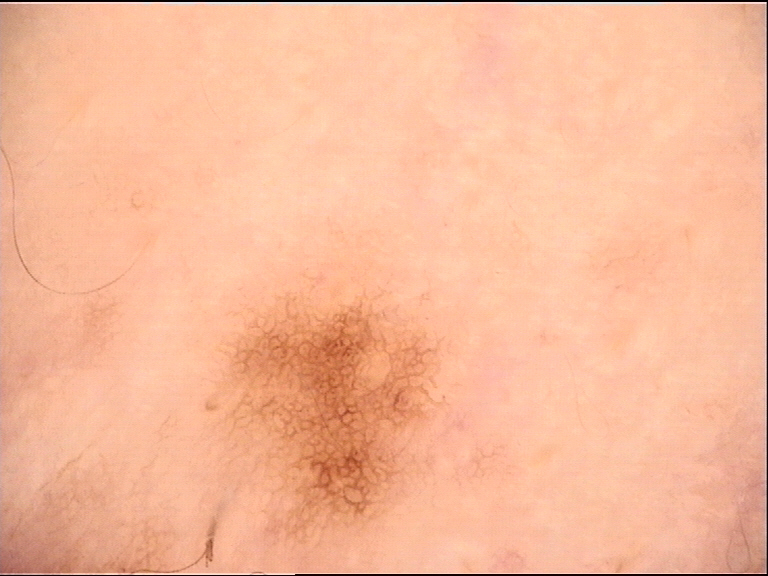class: dysplastic junctional nevus (expert consensus)